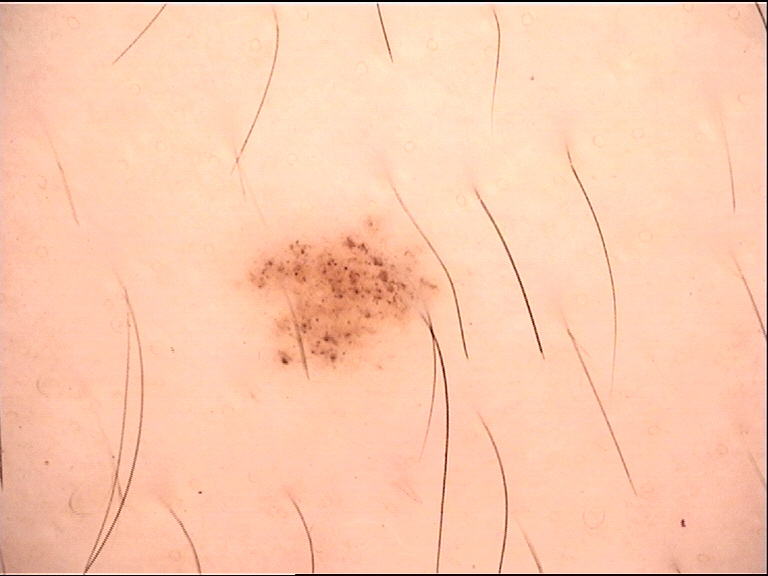Q: What kind of image is this?
A: dermoscopy
Q: How is the lesion classified?
A: banal
Q: What was the diagnostic impression?
A: junctional nevus (expert consensus)